A female patient 48 years old · a clinical photograph showing a skin lesion · collected as part of a research study, without a referral diagnosis.
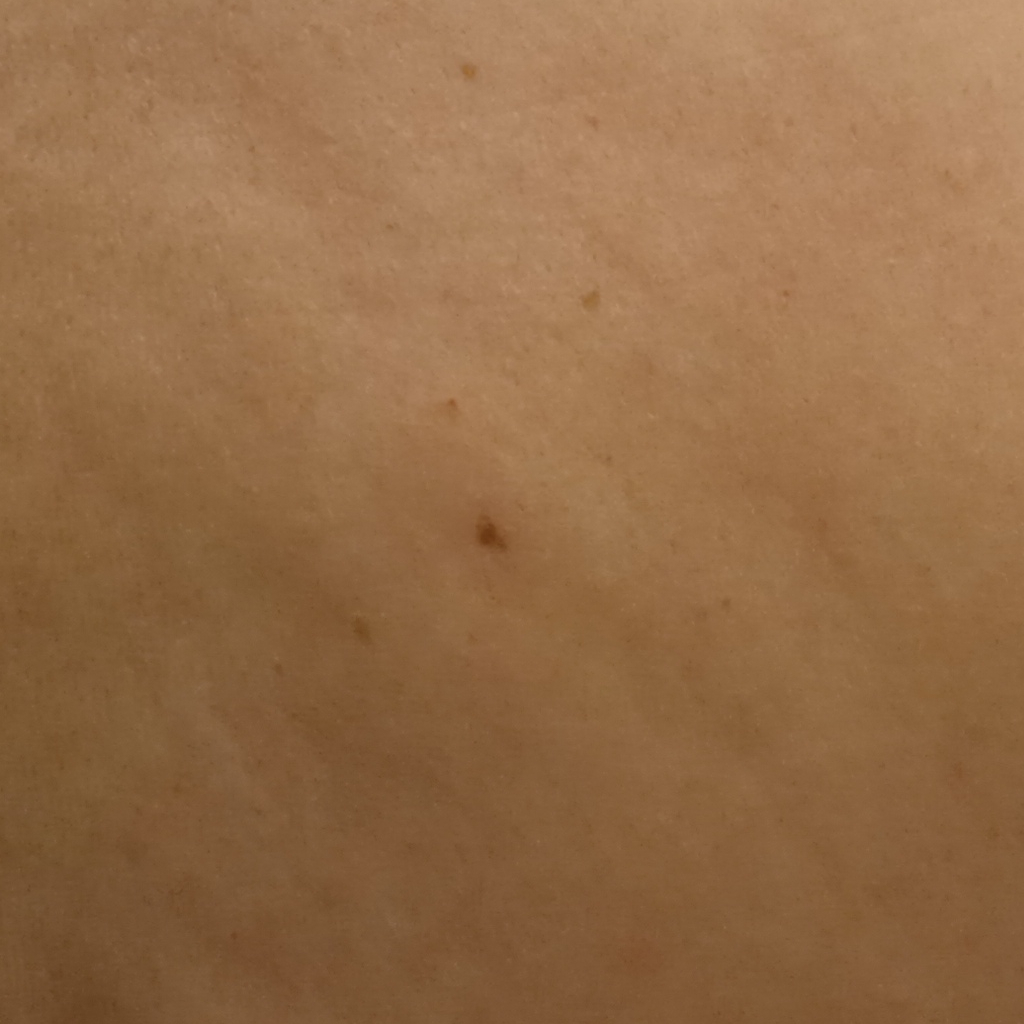* lesion size — 3.7 mm
* diagnosis — melanocytic nevus (dermatologist consensus)